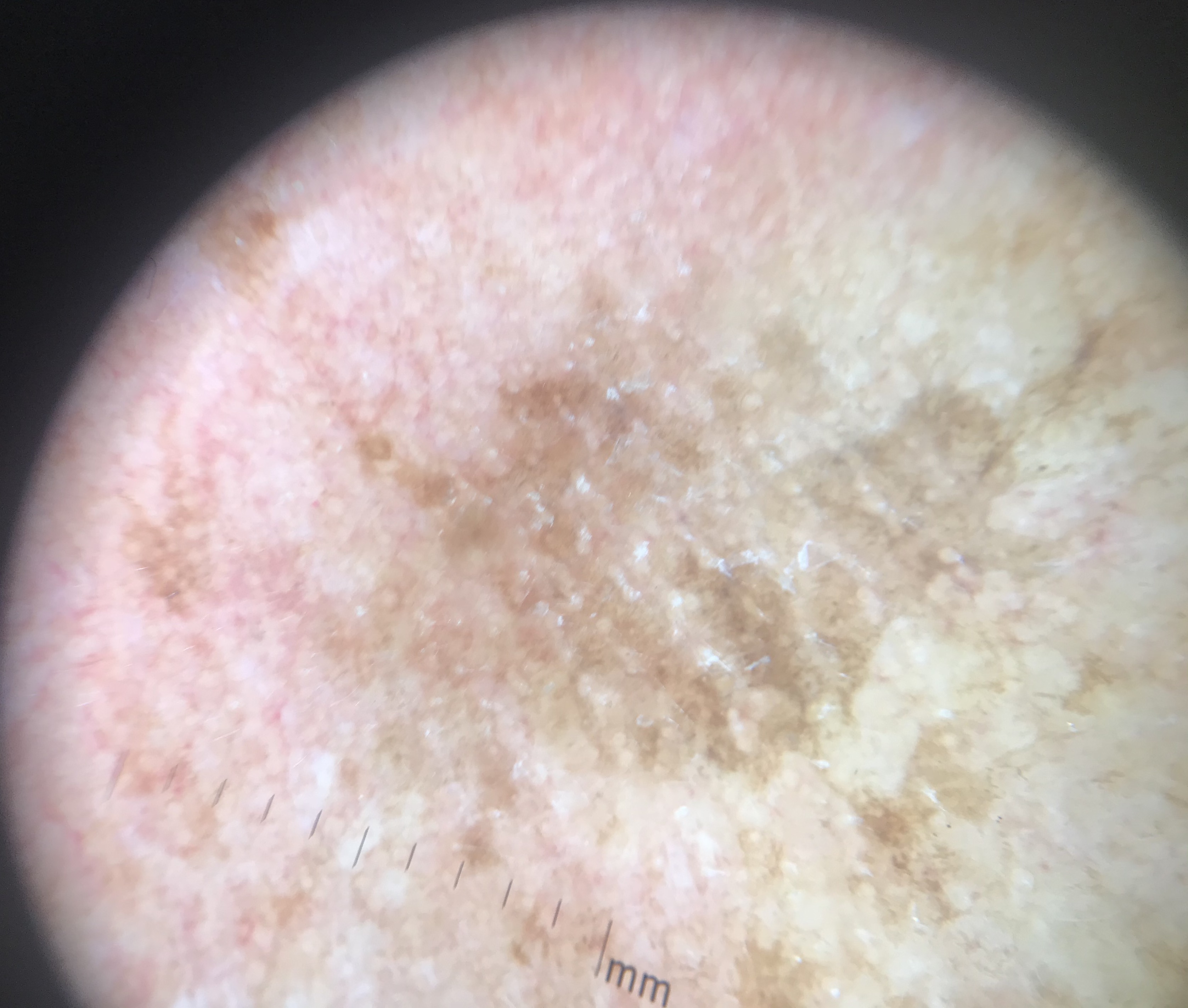Findings:
* subtype — keratinocytic
* class — actinic keratosis (expert consensus)